A dermoscopy image of a single skin lesion.
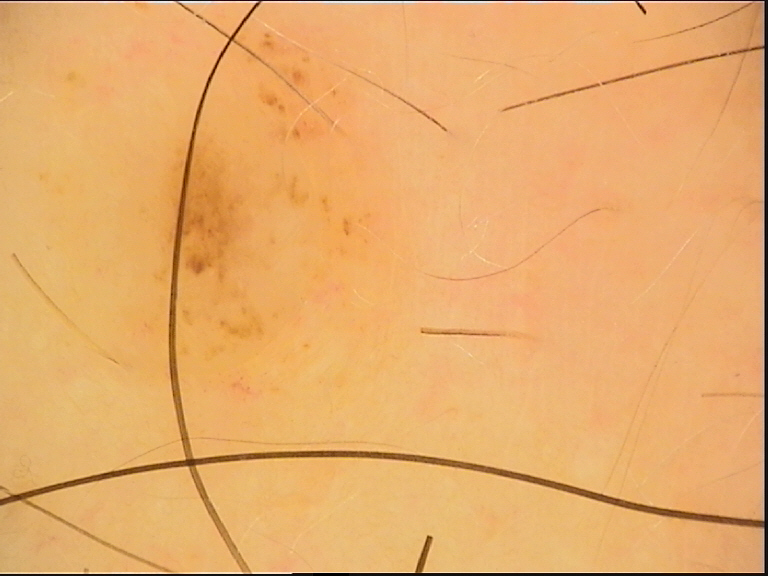category: banal
label: dermal nevus (expert consensus)